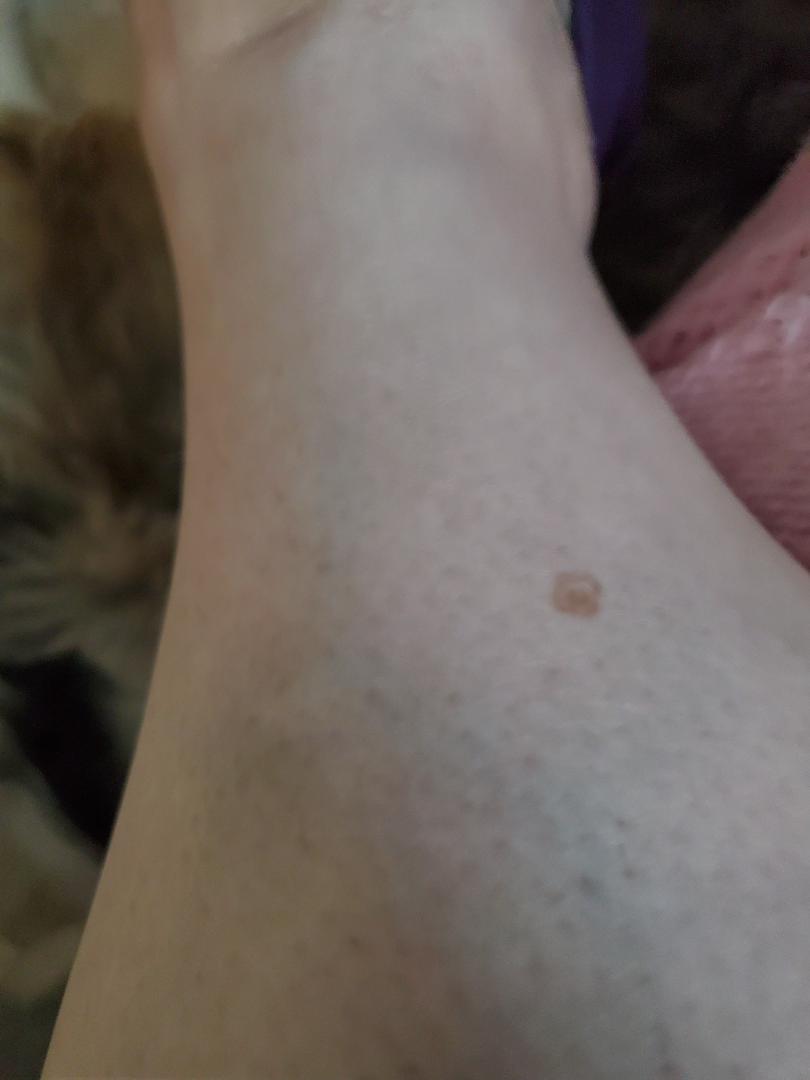Q: How was the photo taken?
A: close-up
Q: What is the dermatologist's impression?
A: single-reviewer assessment: the impression was split between Scar Condition, Atypical Nevus and Melanoma